The back of the hand and arm are involved · close-up view.
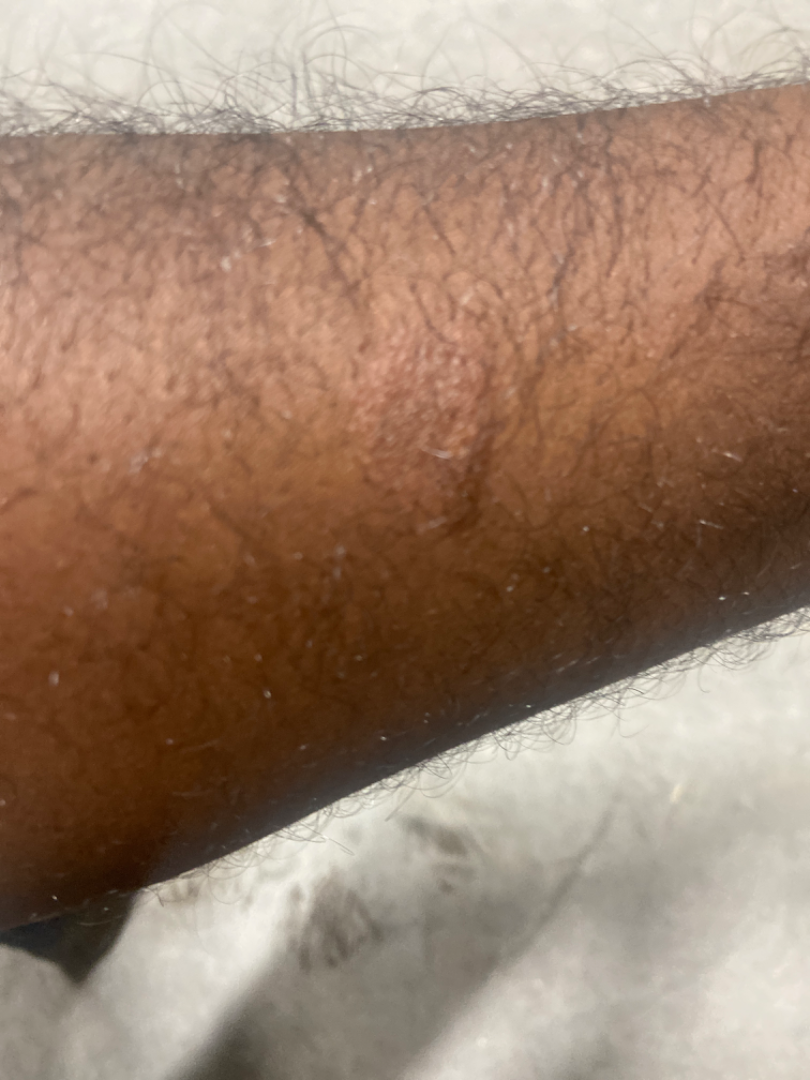No differential diagnosis could be assigned on photographic review.